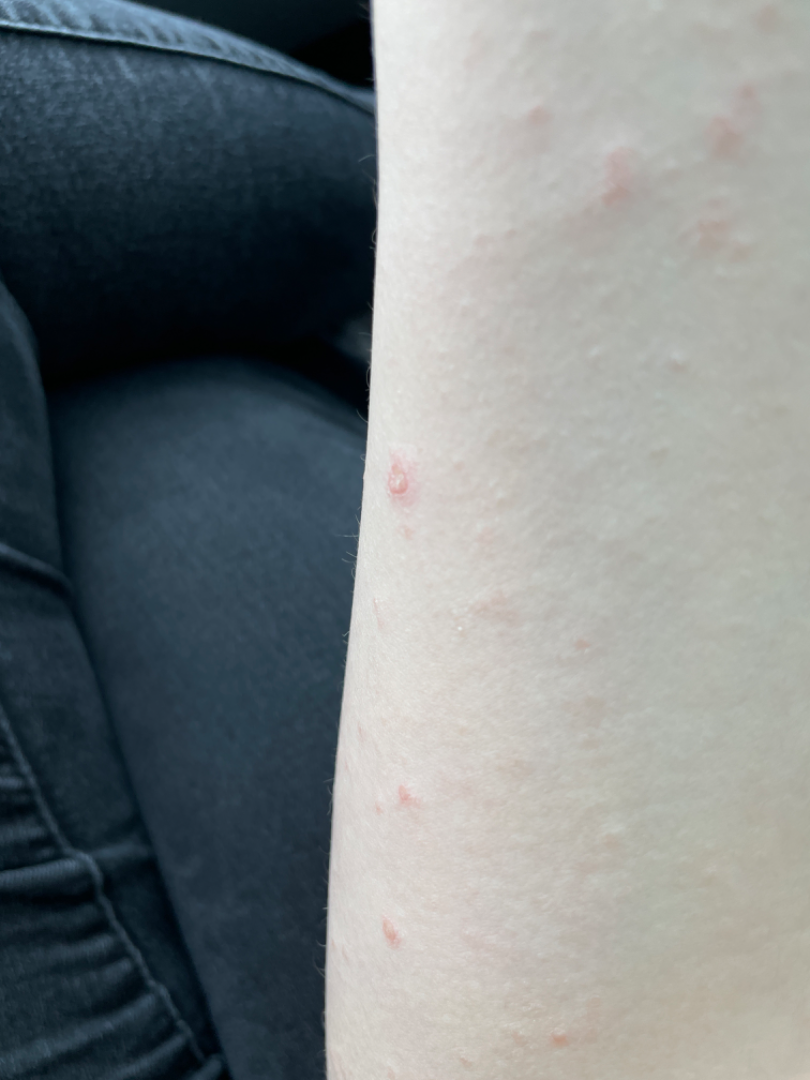assessment = could not be assessed; patient's own categorization = a rash; location = arm; described texture = rough or flaky; associated systemic symptoms = none reported; shot type = at an angle; contributor = female, age 18–29.